Female subject, age 40–49. The photograph was taken at a distance. Located on the arm:
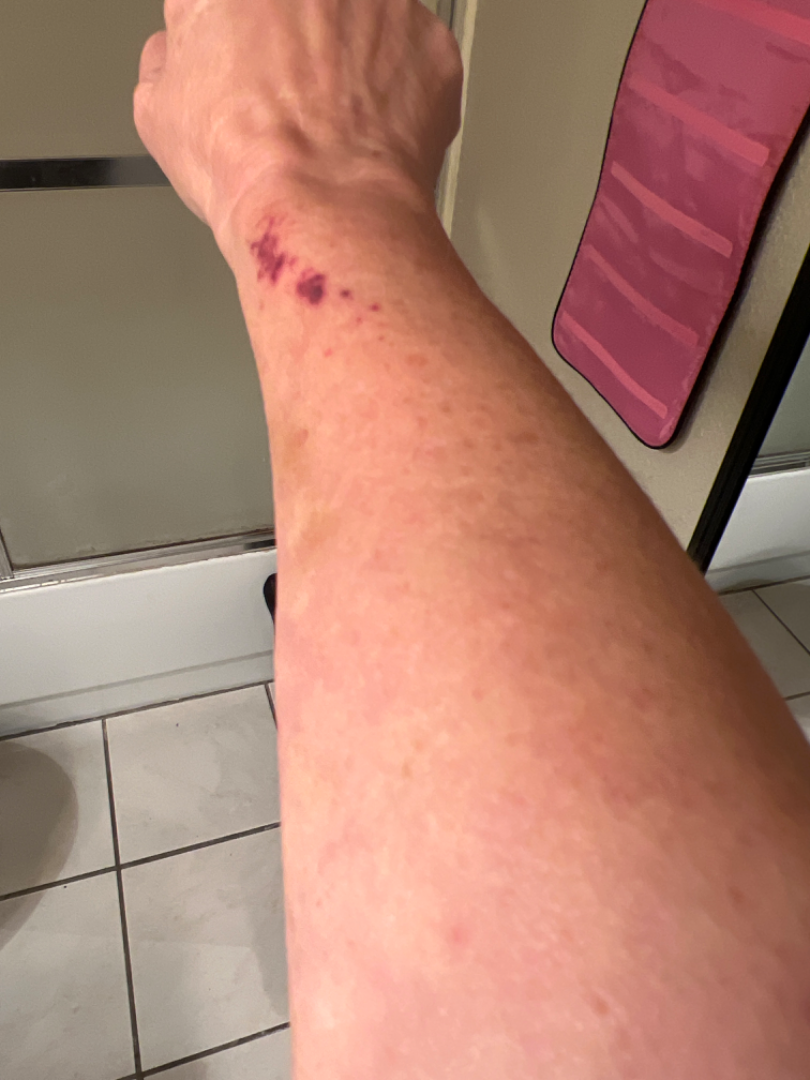The skin condition could not be confidently assessed from this image. Reported duration is less than one week. The contributor reports the lesion is raised or bumpy. Fitzpatrick phototype III; human graders estimated MST 2 or 4 (two reviewer pools disagreed). Self-categorized by the patient as a pigmentary problem.